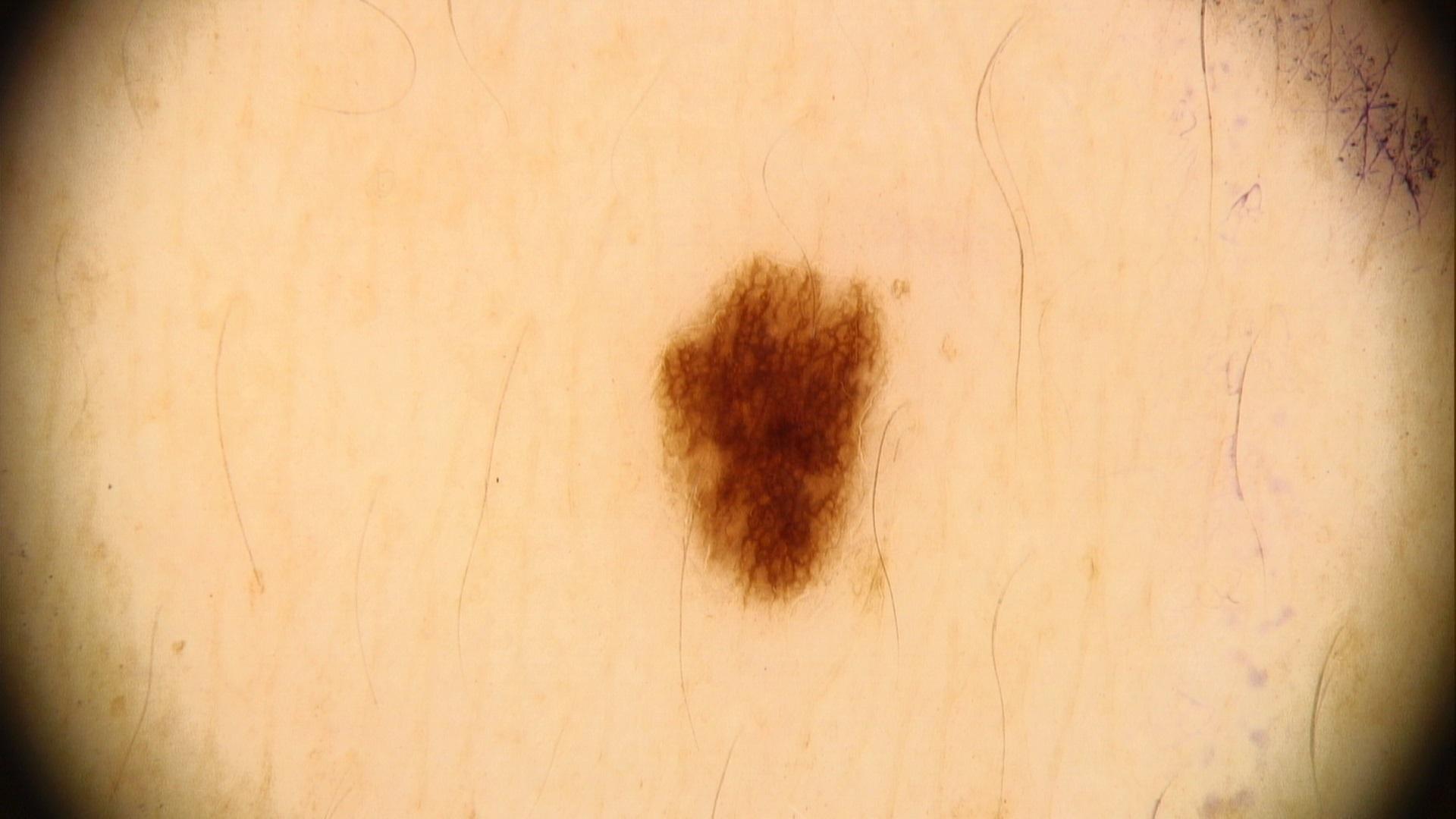A contact-polarized dermoscopy image of a skin lesion.
A female patient aged approximately 35.
The lesion was found on a lower extremity.
Consistent with a nevus.